A skin lesion imaged with a dermatoscope: 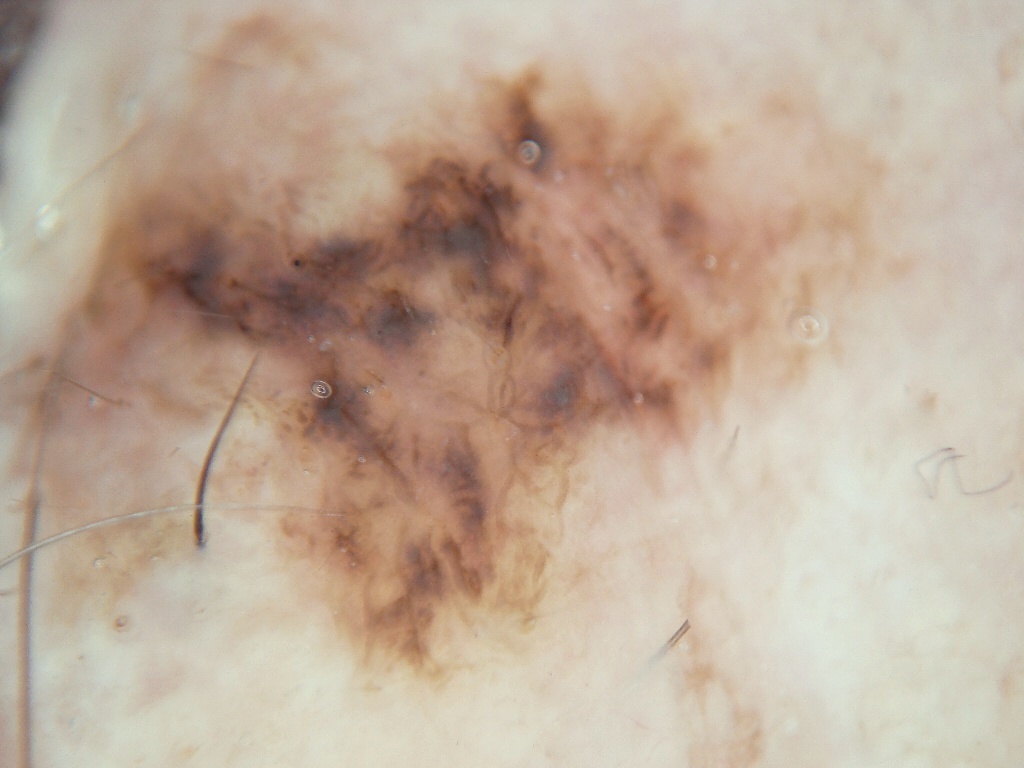{"lesion_location": {"bbox_xyxy": [5, 14, 919, 732]}, "dermoscopic_features": {"present": [], "absent": ["globules", "streaks"]}, "diagnosis": {"malignancy": "malignant", "provenance": "histopathology"}}